The lesion involves the back of the hand, arm, leg and head or neck · the subject is a male aged 40–49 · the lesion is described as raised or bumpy · a close-up photograph · reported duration is three to twelve months:
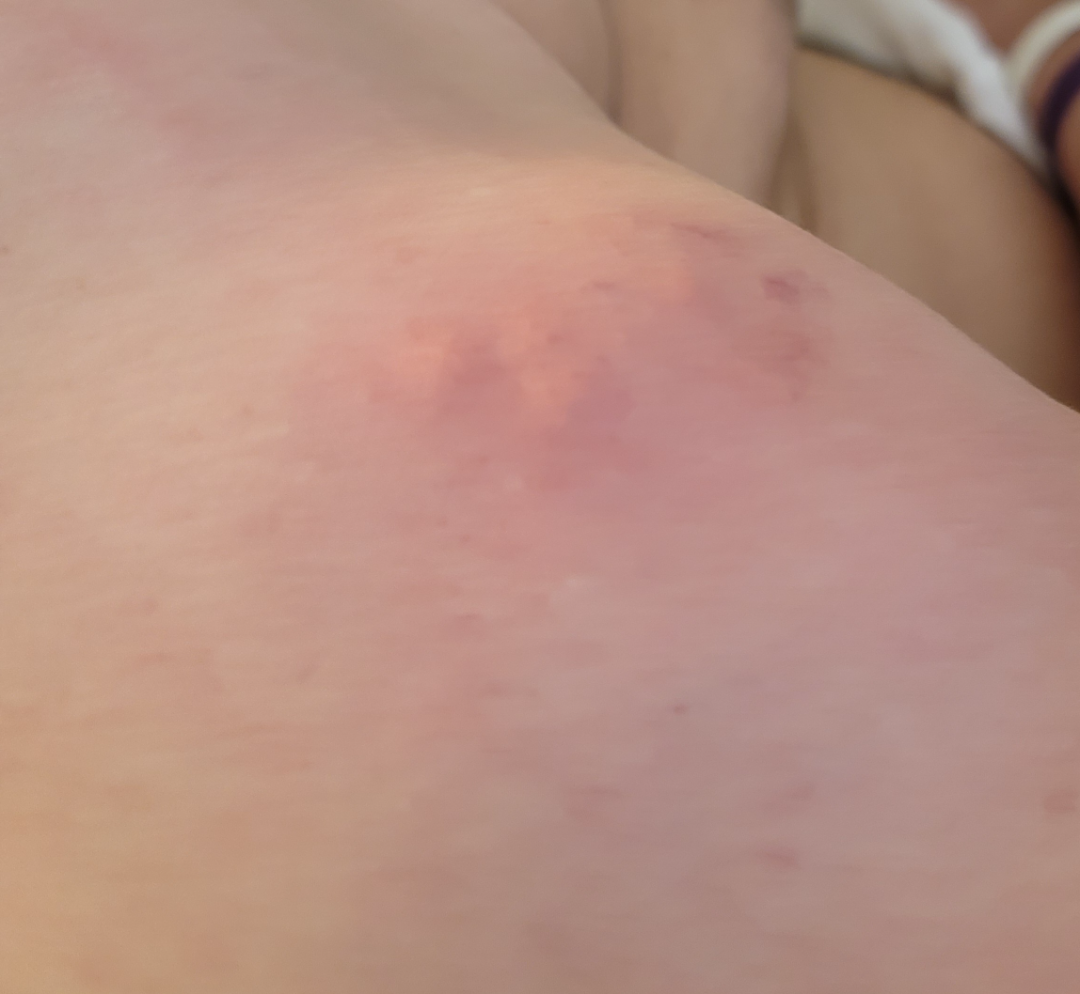Review: Abscess, Cellulitis and Cyst were each considered, in no particular order.